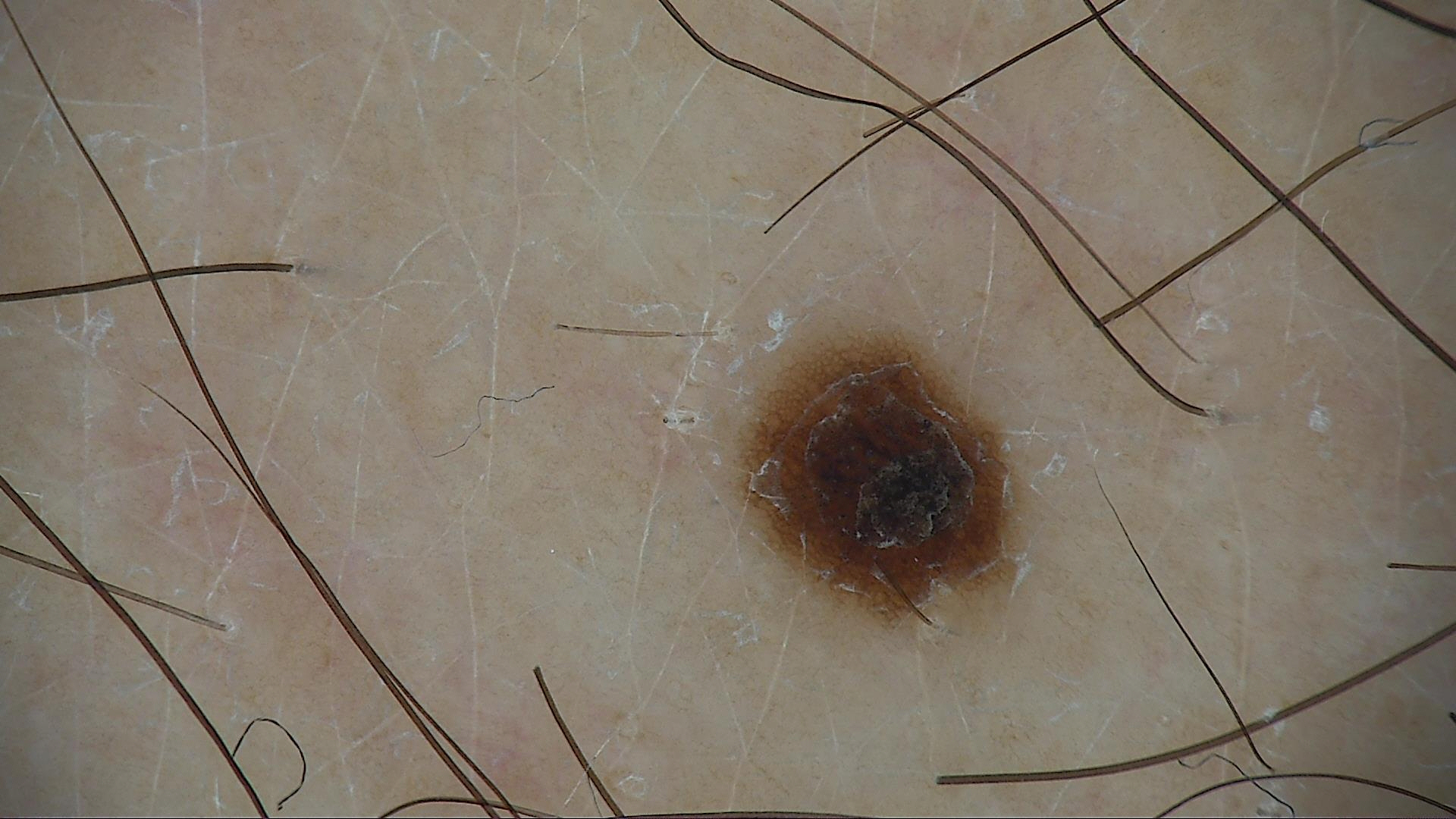Case: A dermoscopy image of a single skin lesion. Conclusion: Consistent with a benign lesion — a dysplastic junctional nevus.